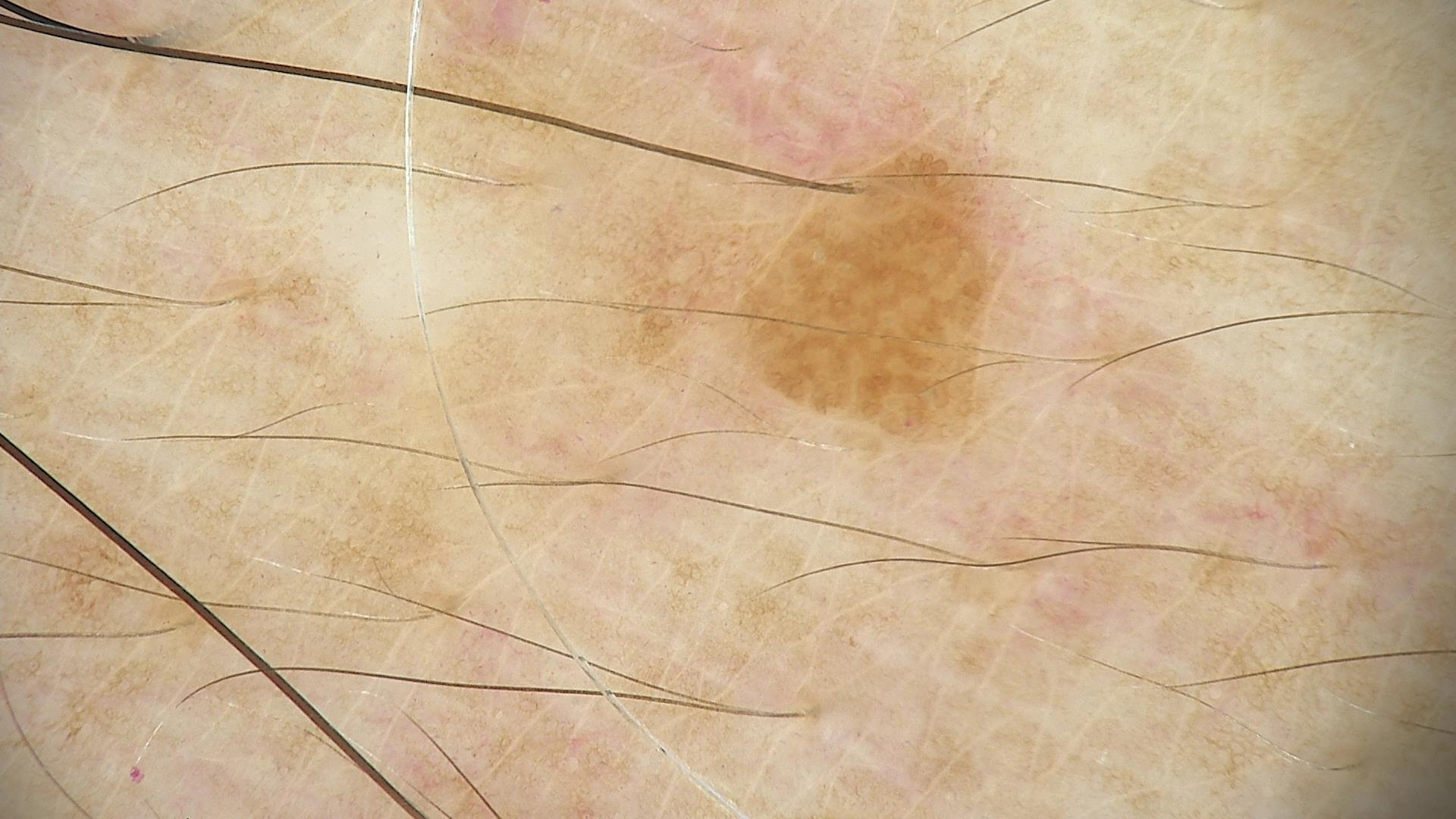Q: What kind of image is this?
A: dermoscopy
Q: What was the diagnostic impression?
A: seborrheic keratosis (expert consensus)